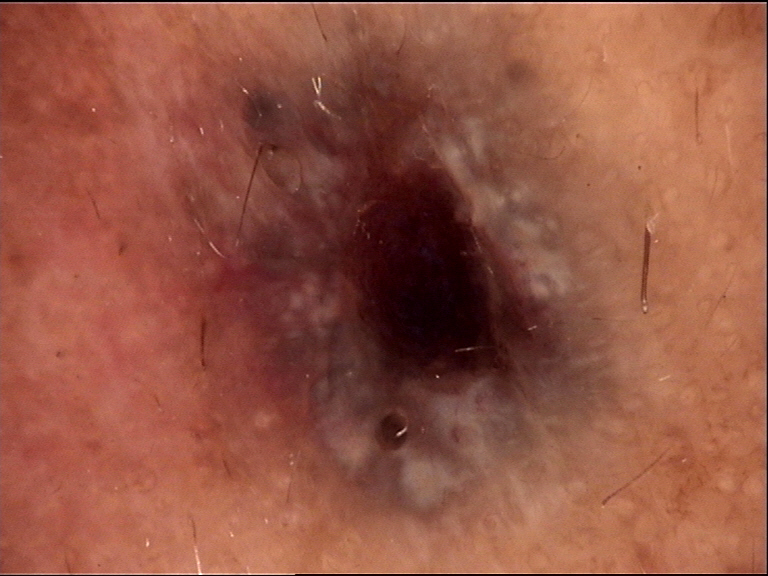Findings:
- modality: dermatoscopy
- class: basal cell carcinoma (biopsy-proven)